The patient is a male aged 50–59. The photograph was taken at a distance: 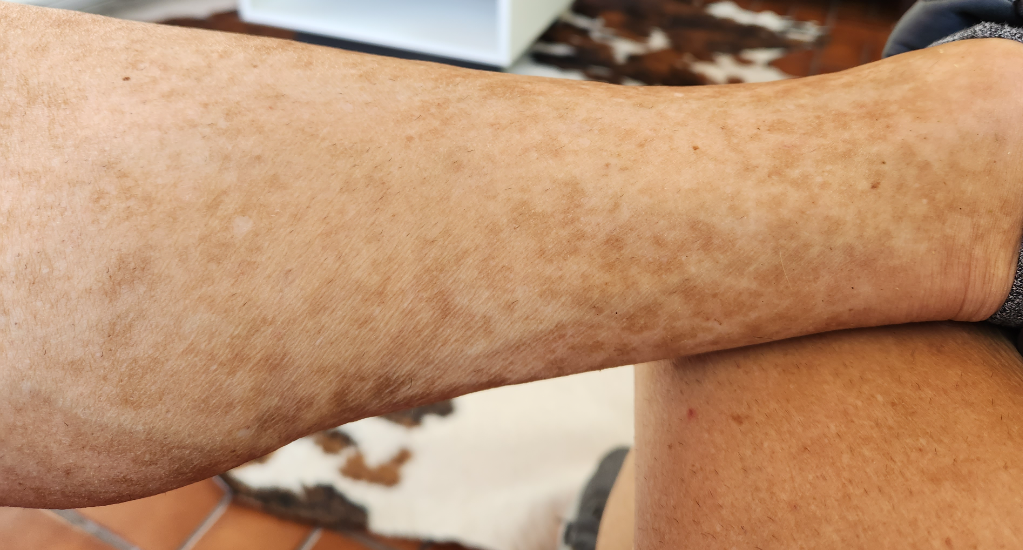Patient information: Fitzpatrick skin type III. Review: The reviewing dermatologist's impression was: consistent with Pigmented purpuric eruption.